The affected area is the back of the hand. The photograph is a close-up of the affected area:
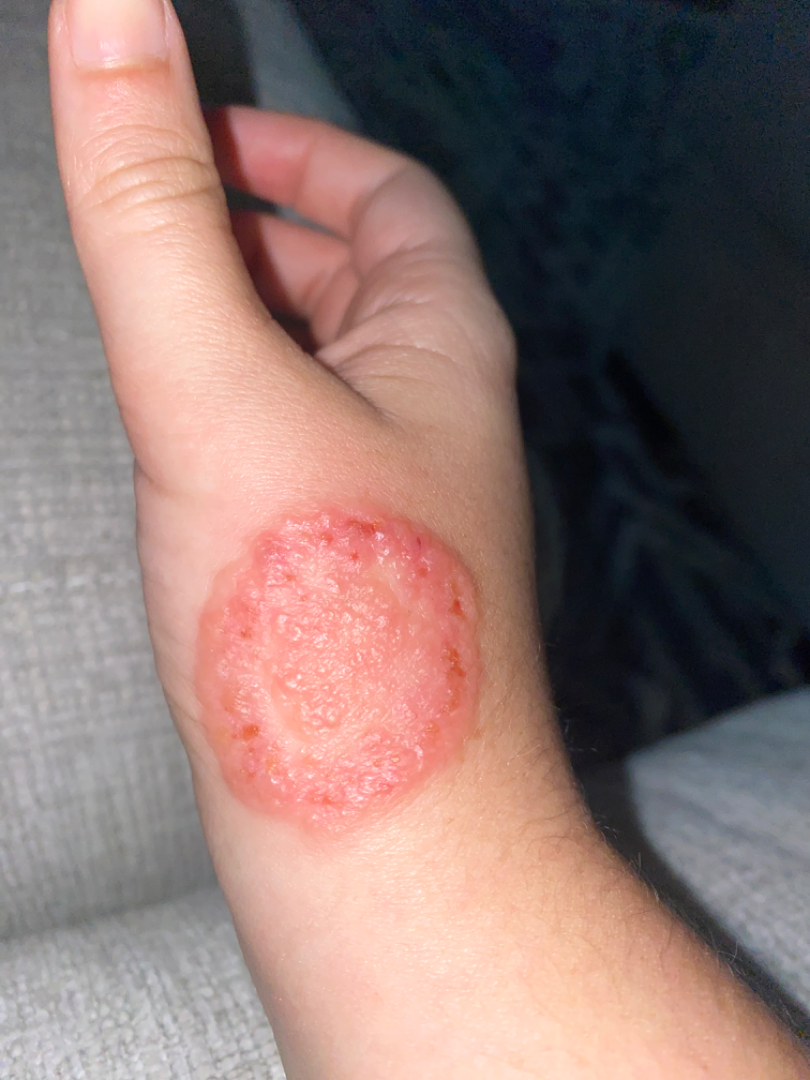Symptoms reported: pain, bothersome appearance, itching, enlargement and burning.
The lesion is described as fluid-filled and raised or bumpy.
Reported duration is one to four weeks.
The differential, in no particular order, includes Impetigo, Fungal dermatosis and Molluscum Contagiosum.